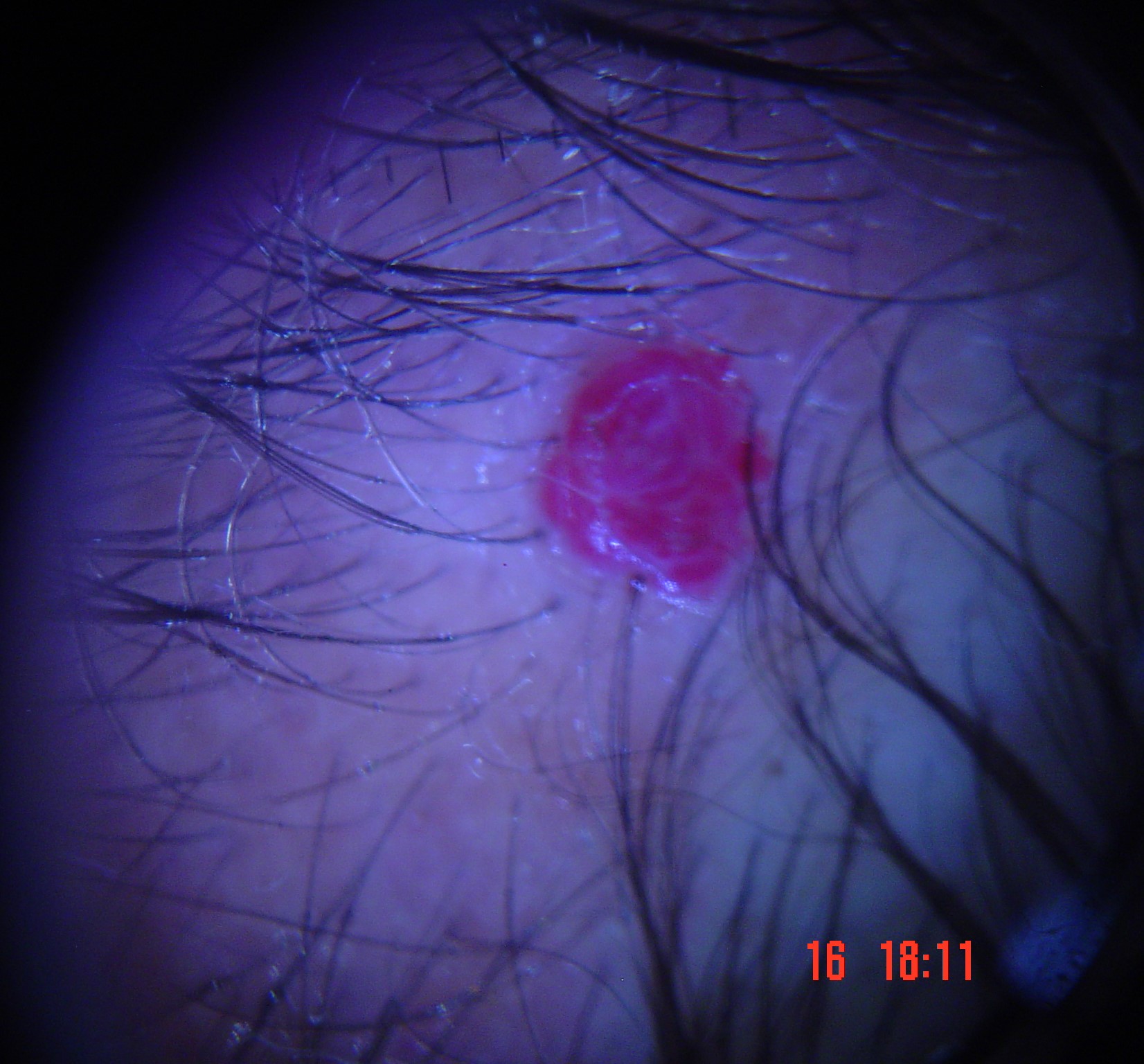Labeled as a benign, vascular lesion — a hemangioma.